A dermoscopic image of a skin lesion · the patient describes having few moles overall · acquired for a research image collection, with no referral diagnosis · a female subject 48 years old · the patient reports a family history of skin cancer and a history of sunbed use: 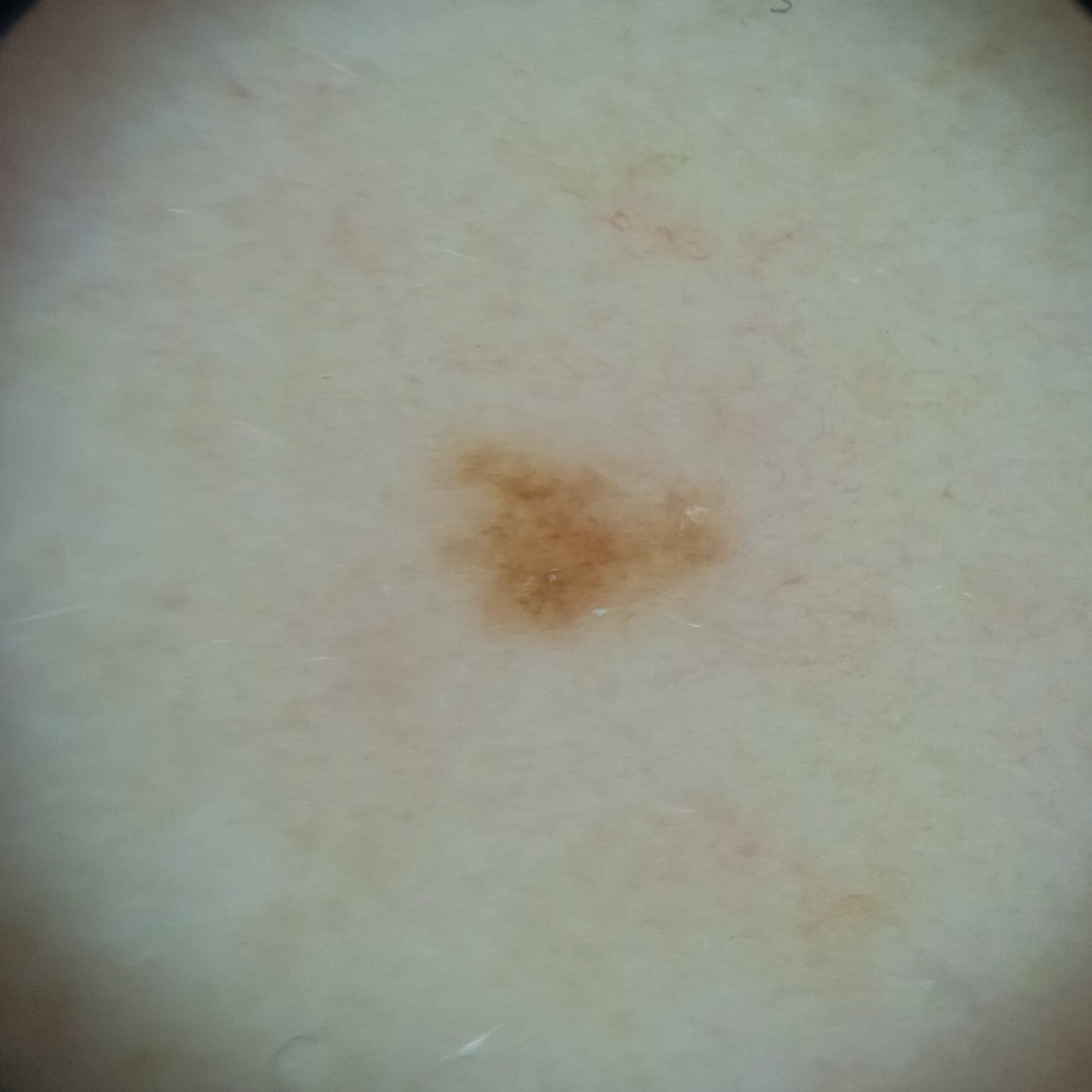* assessment · melanocytic nevus (dermatologist consensus)